A dermoscopic image of a skin lesion: 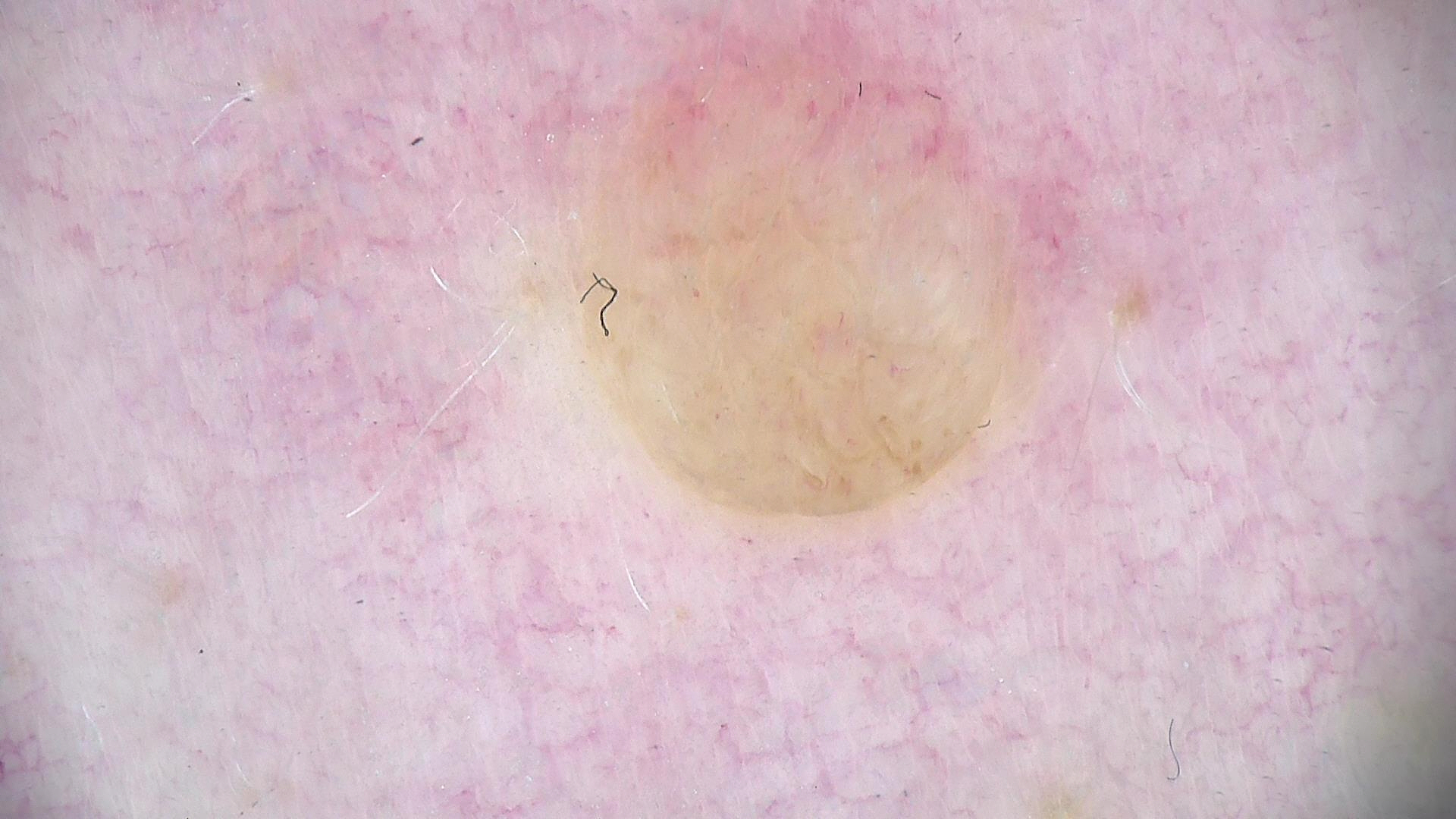assessment=dermal nevus (expert consensus).